A dermoscopic close-up of a skin lesion:
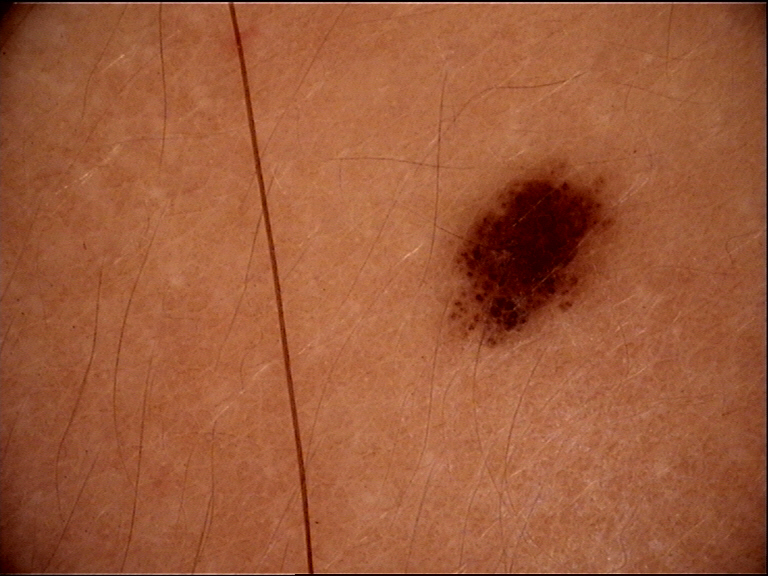The architecture is that of a banal lesion. Classified as a junctional nevus.